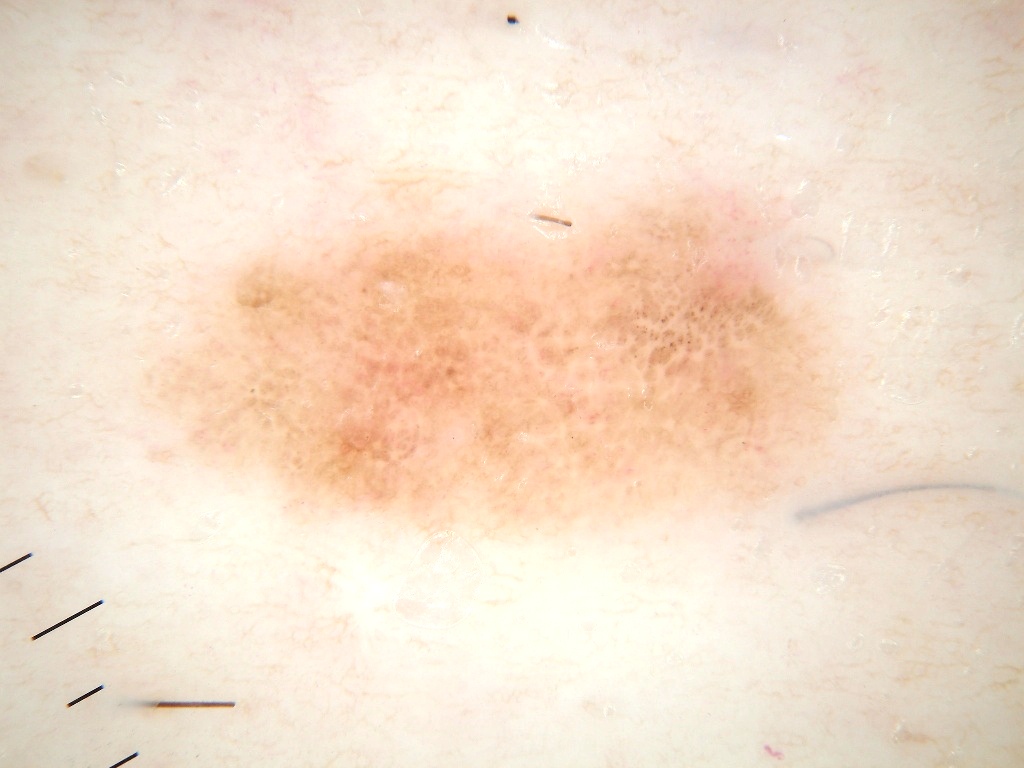<dermoscopy>
  <image>
    <modality>dermoscopy</modality>
  </image>
  <patient>
    <sex>male</sex>
    <age_approx>45</age_approx>
  </patient>
  <dermoscopic_features>
    <present>negative network, globules</present>
    <absent>pigment network, milia-like cysts, streaks</absent>
  </dermoscopic_features>
  <lesion_extent>
    <approx_field_fraction_pct>22</approx_field_fraction_pct>
  </lesion_extent>
  <lesion_location>
    <bbox_xyxy>144, 185, 843, 528</bbox_xyxy>
  </lesion_location>
  <diagnosis>
    <name>melanocytic nevus</name>
    <malignancy>benign</malignancy>
    <lineage>melanocytic</lineage>
    <provenance>clinical</provenance>
  </diagnosis>
</dermoscopy>